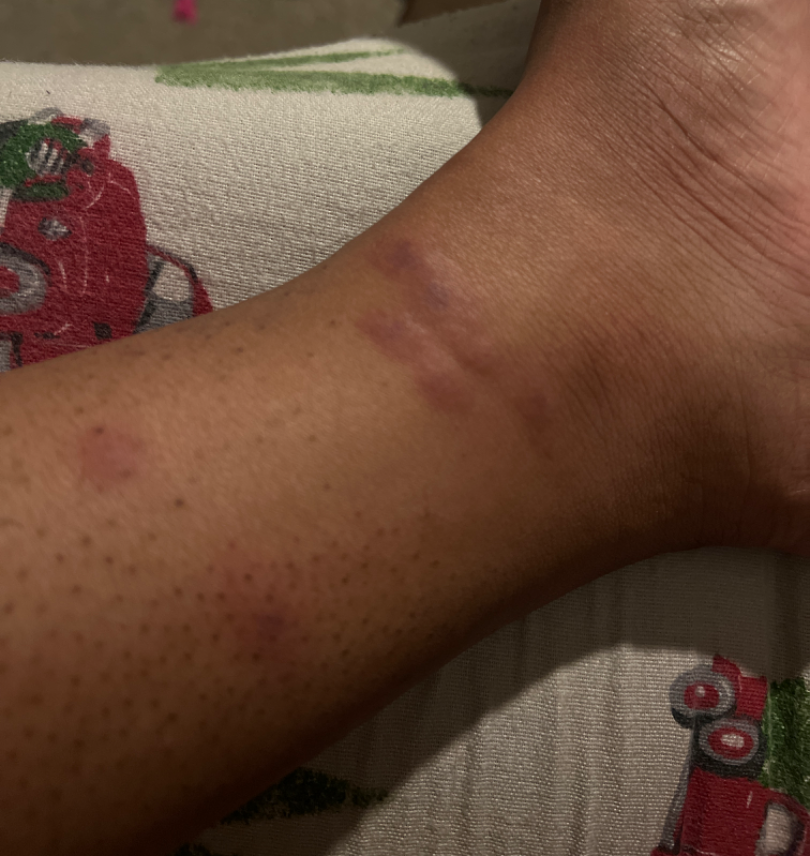Located on the leg. An image taken at a distance. The contributor is 18–29, female. On remote dermatologist review, the leading impression is Allergic Contact Dermatitis.